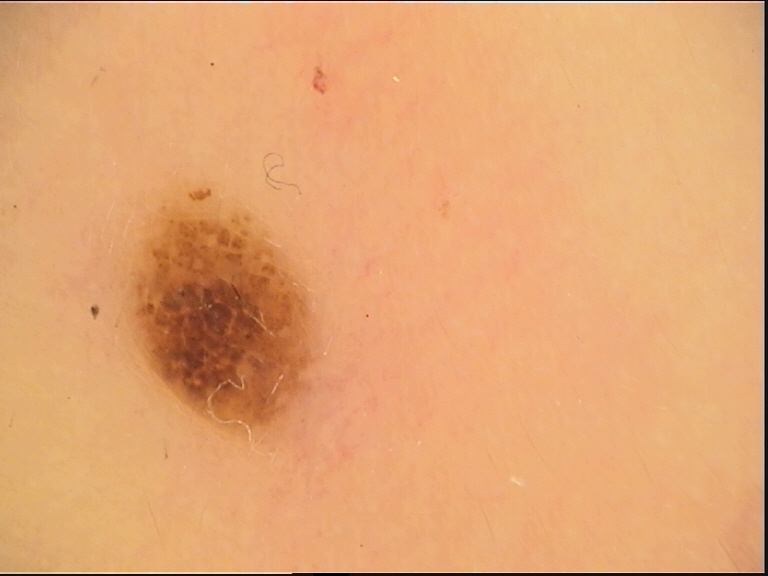A dermoscopic image of a skin lesion. The morphology is that of a banal lesion. Labeled as a compound nevus.